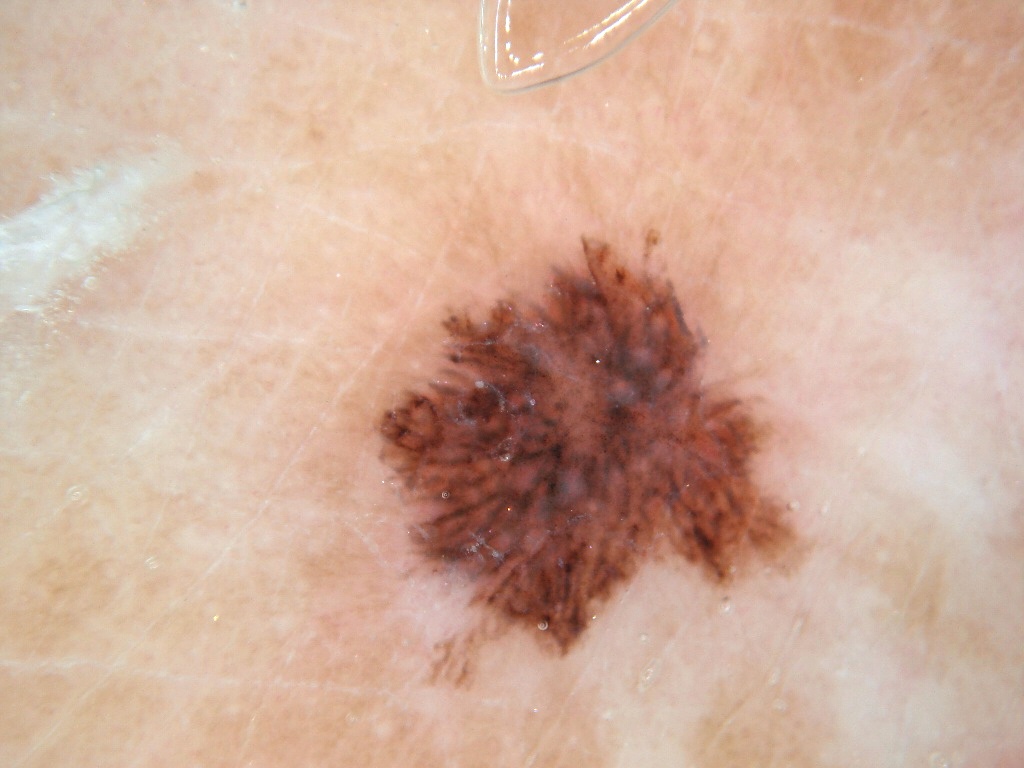Findings:
Dermoscopy of a skin lesion. In (x1, y1, x2, y2) order, the lesion occupies the region 356, 235, 803, 685. The lesion occupies roughly 15% of the field. On dermoscopy, the lesion shows streaks.
Impression:
Consistent with a benign skin lesion.